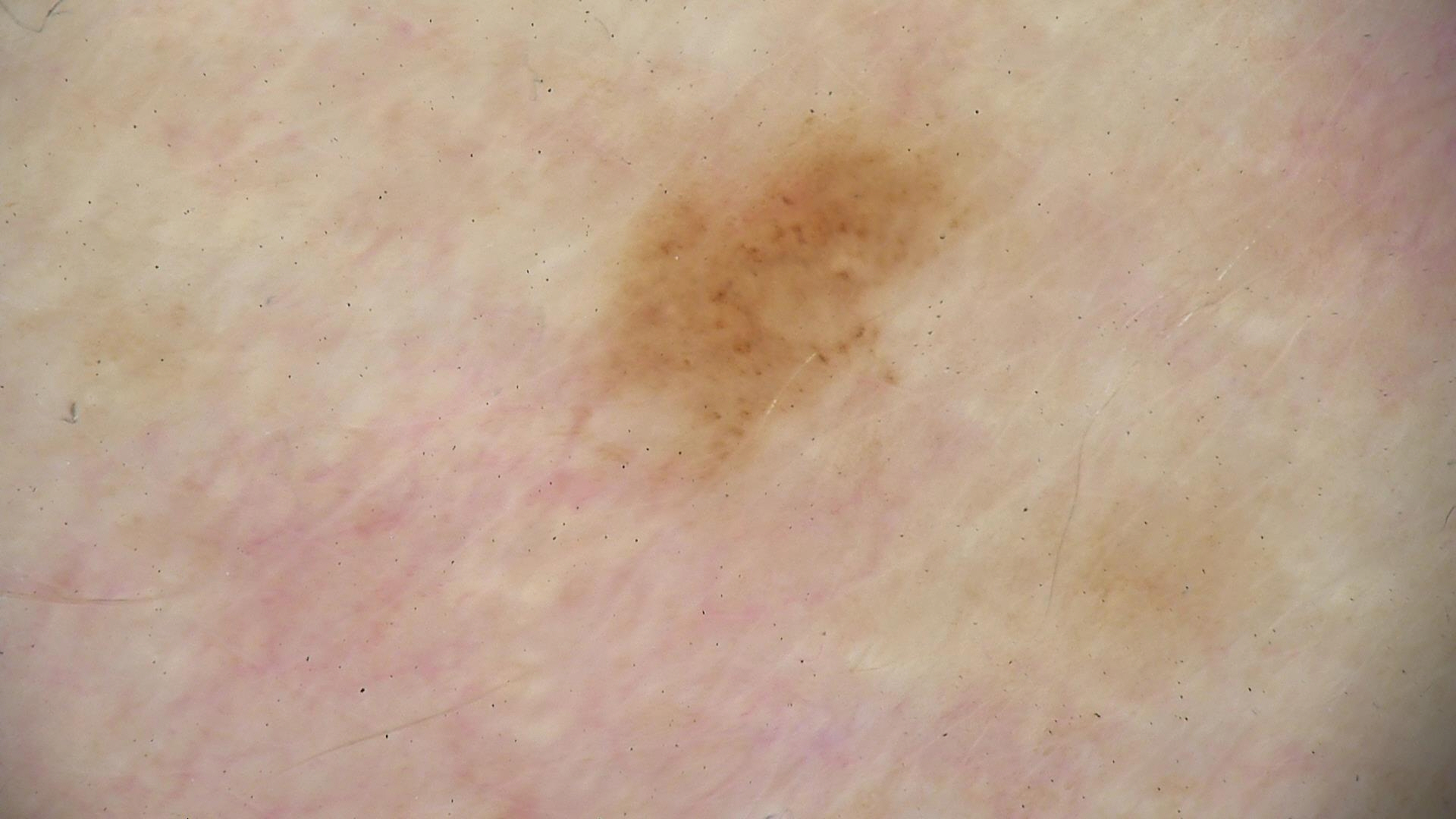Case:
- imaging · dermoscopy
- diagnosis · dysplastic junctional nevus (expert consensus)